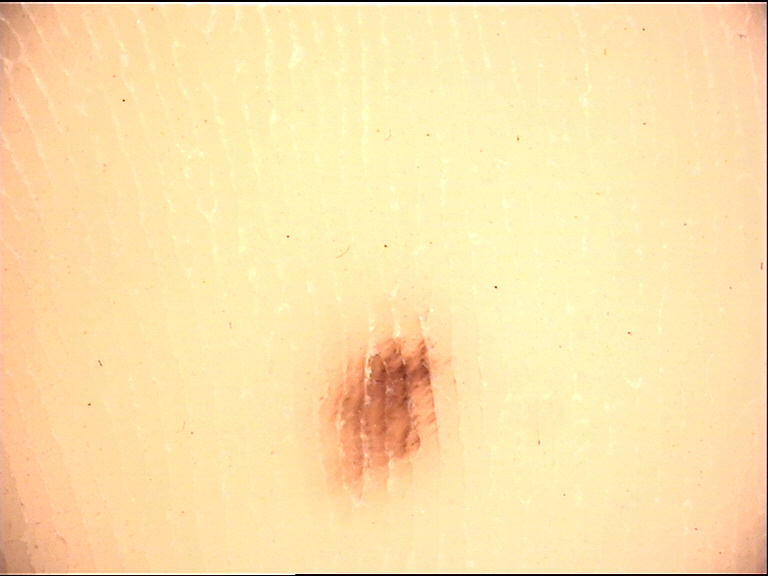Case:
Dermoscopy of a skin lesion. The morphology is that of a banal lesion.
Conclusion:
Consistent with an acral junctional nevus.